A dermoscopic close-up of a skin lesion · the patient was assessed as Fitzpatrick skin type II · a male subject aged 68-72.
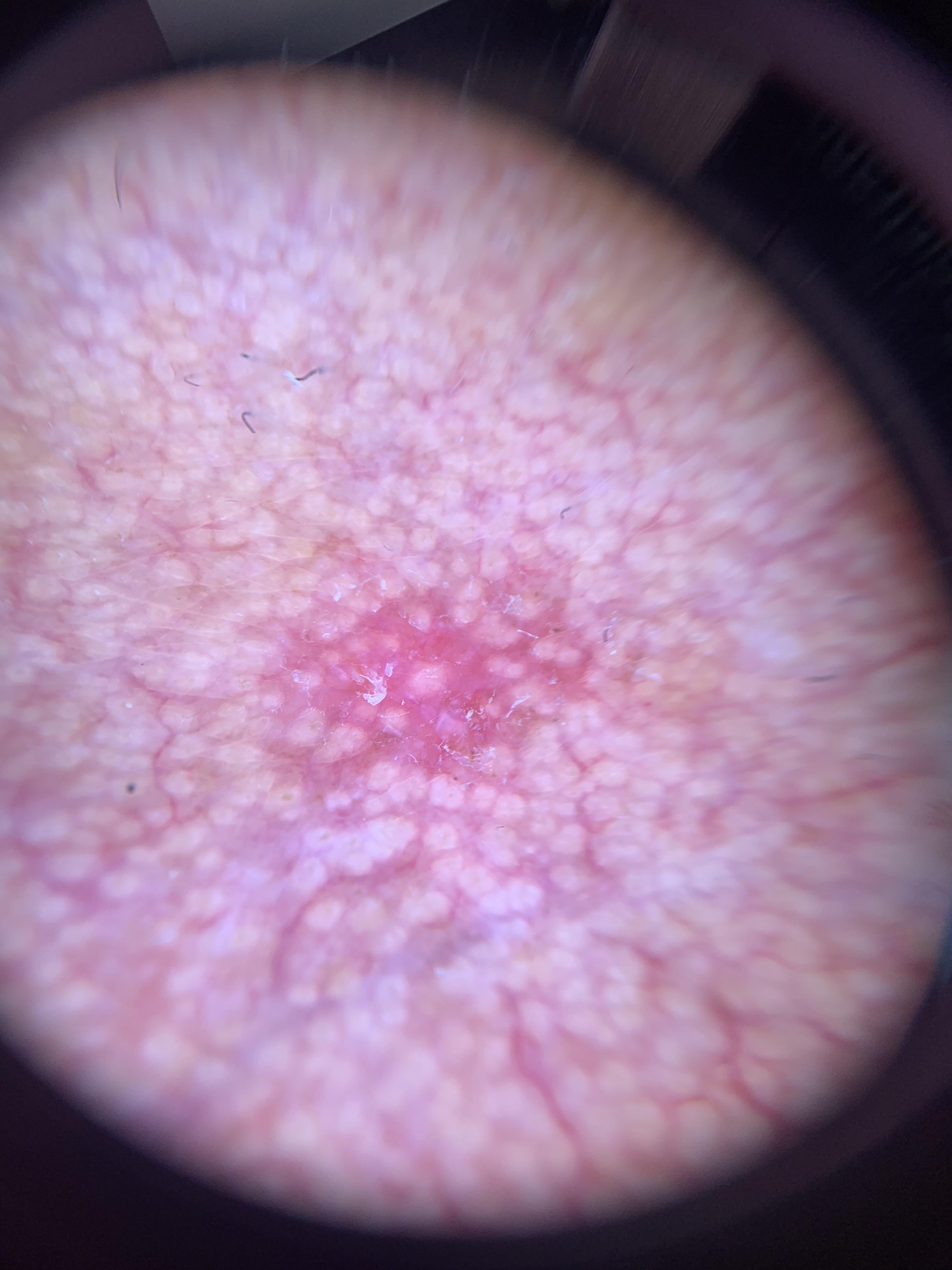pathology=Basal cell carcinoma (biopsy-proven).